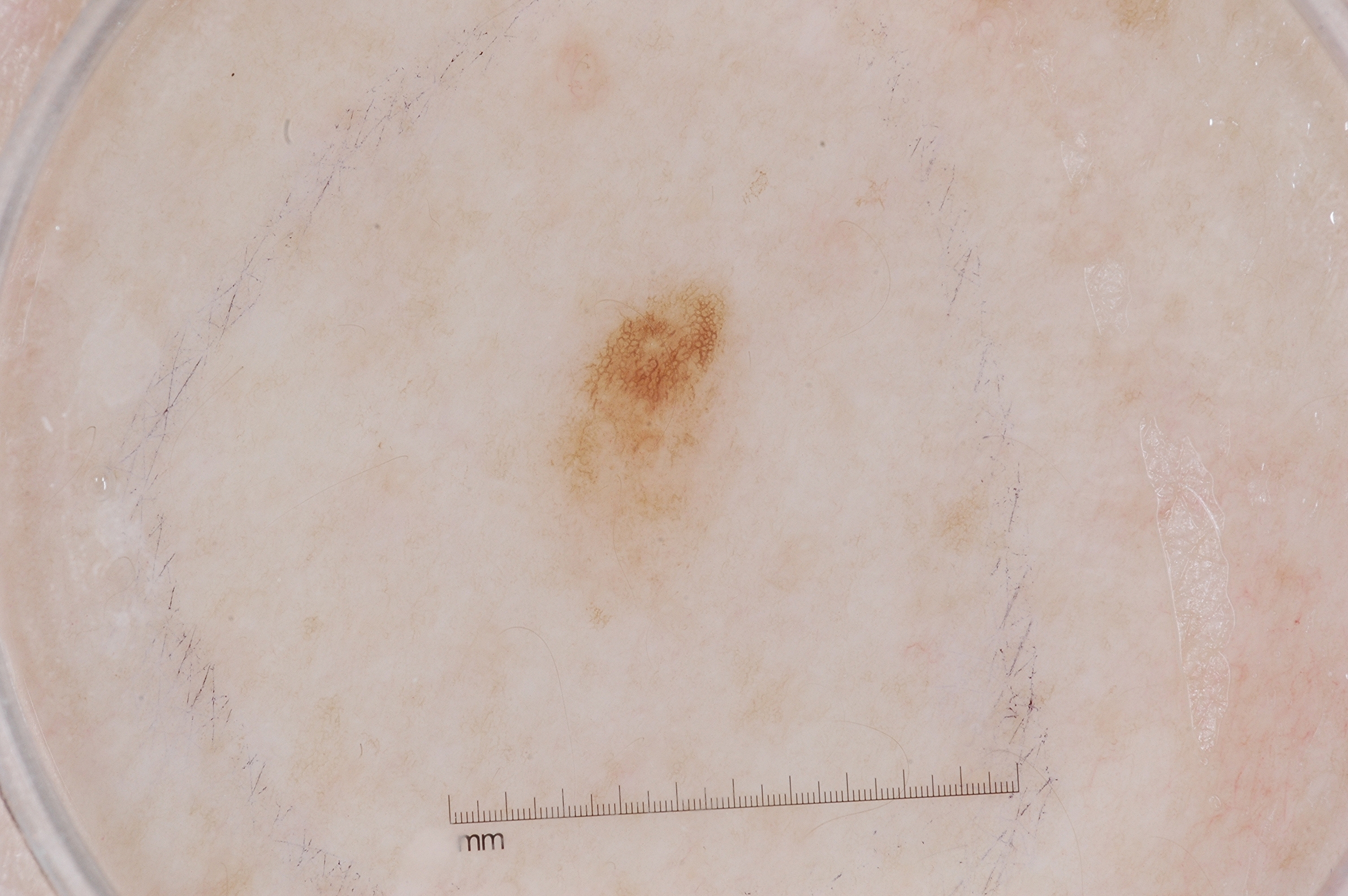This is a dermoscopic photograph of a skin lesion. With coordinates (x1, y1, x2, y2), the lesion's extent is [543,273,746,575]. Consistent with a melanocytic nevus, a benign skin lesion.